Located on the arm, reported lesion symptoms include itching, present for less than one week, close-up view, the patient is female, the patient reports the lesion is raised or bumpy:
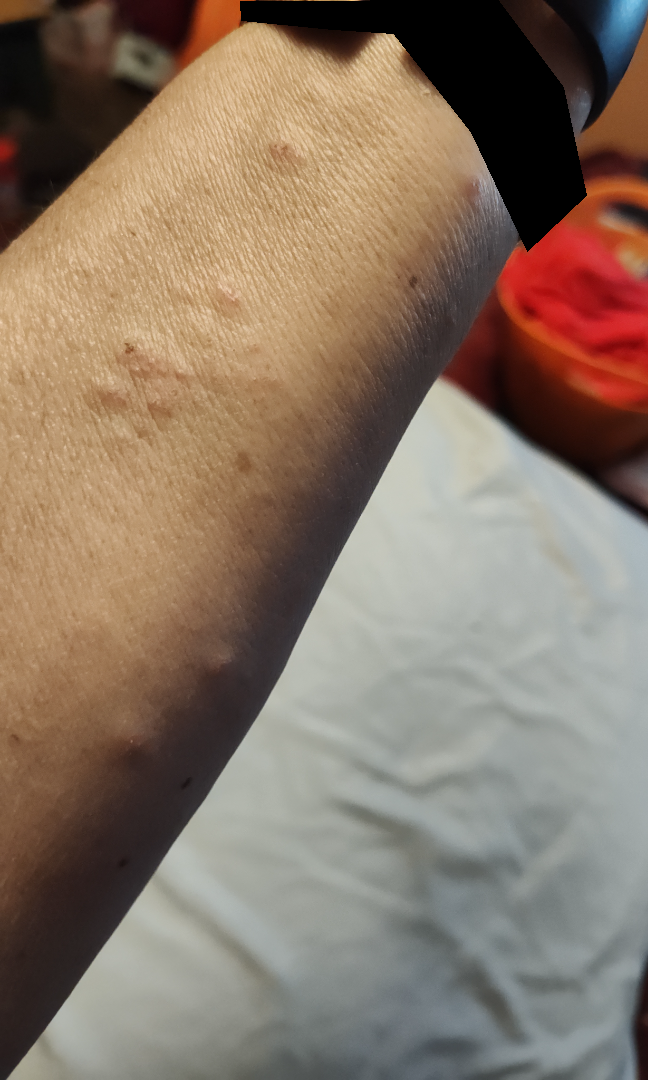Assessment:
The reviewing panel's impression was: the differential, in no particular order, includes Granuloma annulare, Skin and soft tissue atypical mycobacterial infection, Eczema and Allergic Contact Dermatitis.